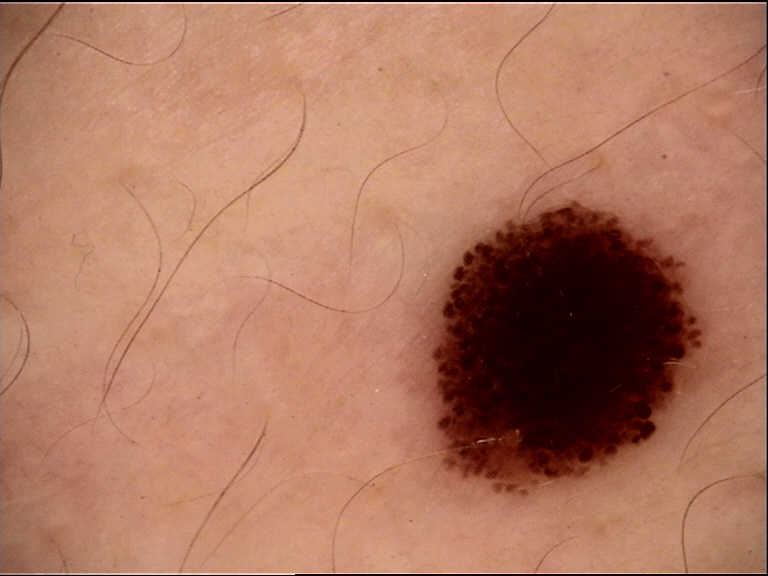{
  "image": "dermatoscopy",
  "lesion_type": {
    "main_class": "dysplastic",
    "pattern": "junctional"
  },
  "diagnosis": {
    "name": "Spitz/Reed nevus",
    "code": "srjd",
    "malignancy": "benign",
    "super_class": "melanocytic",
    "confirmation": "expert consensus"
  }
}